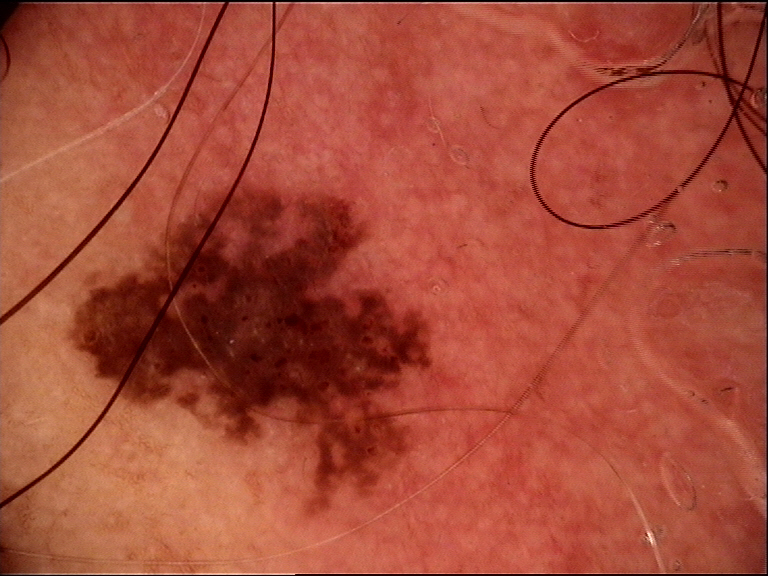Biopsy-confirmed as a lentigo maligna.